A dermoscopy image of a single skin lesion.
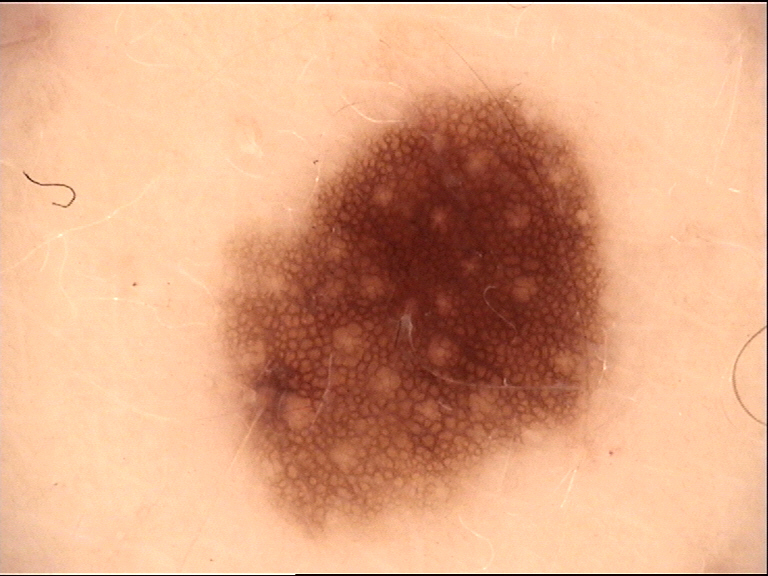Case:
– assessment — dysplastic junctional nevus (expert consensus)